A skin lesion imaged with a dermatoscope · the patient describes having a moderate number of moles · a female subject 75 years of age · the patient says their skin tans without first burning · acquired for a research image collection, with no referral diagnosis · the patient reports a personal history of cancer and a personal history of skin cancer.
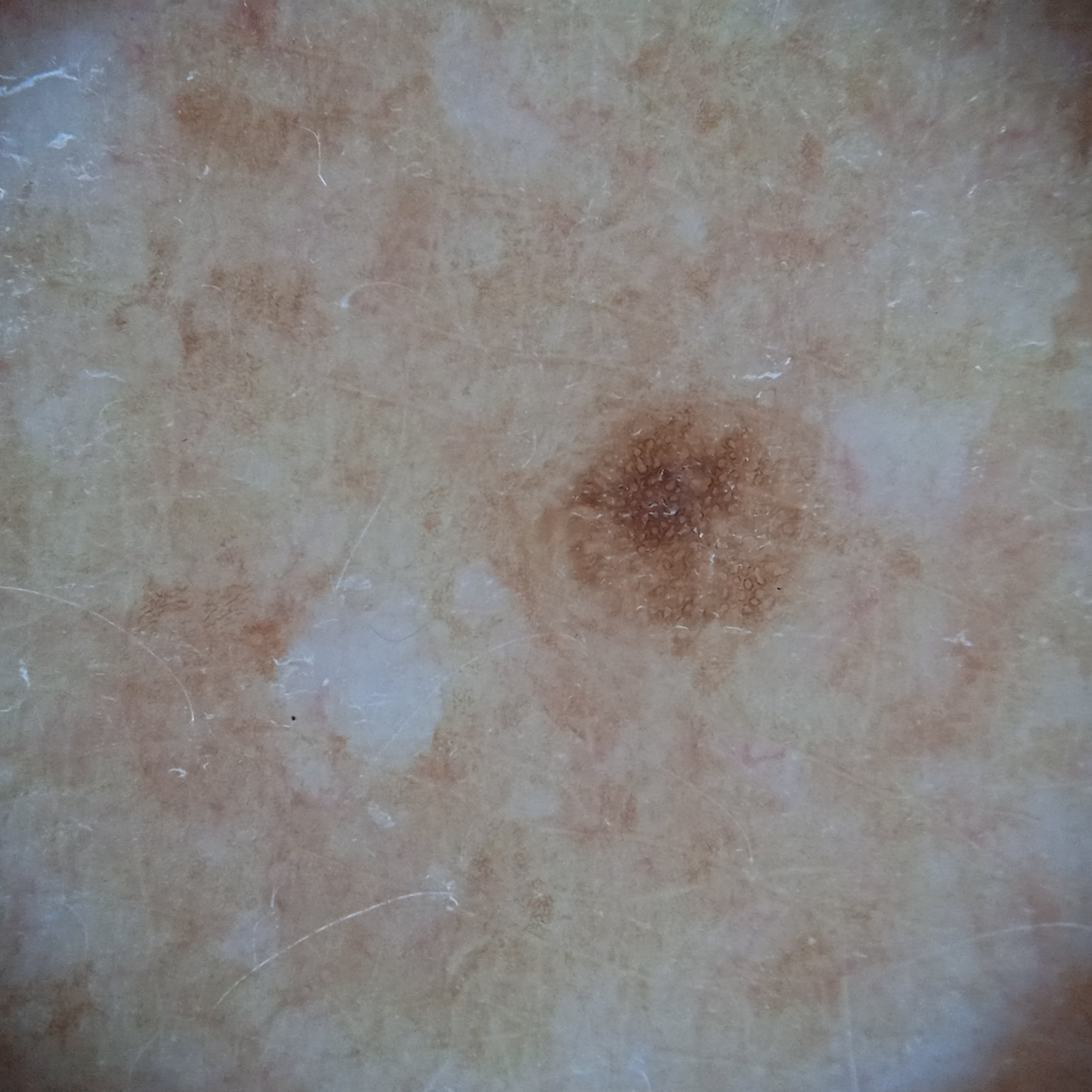anatomic site: the back; size: 2.7 mm; assessment: melanocytic nevus (dermatologist consensus).